A dermoscopic image of a skin lesion: 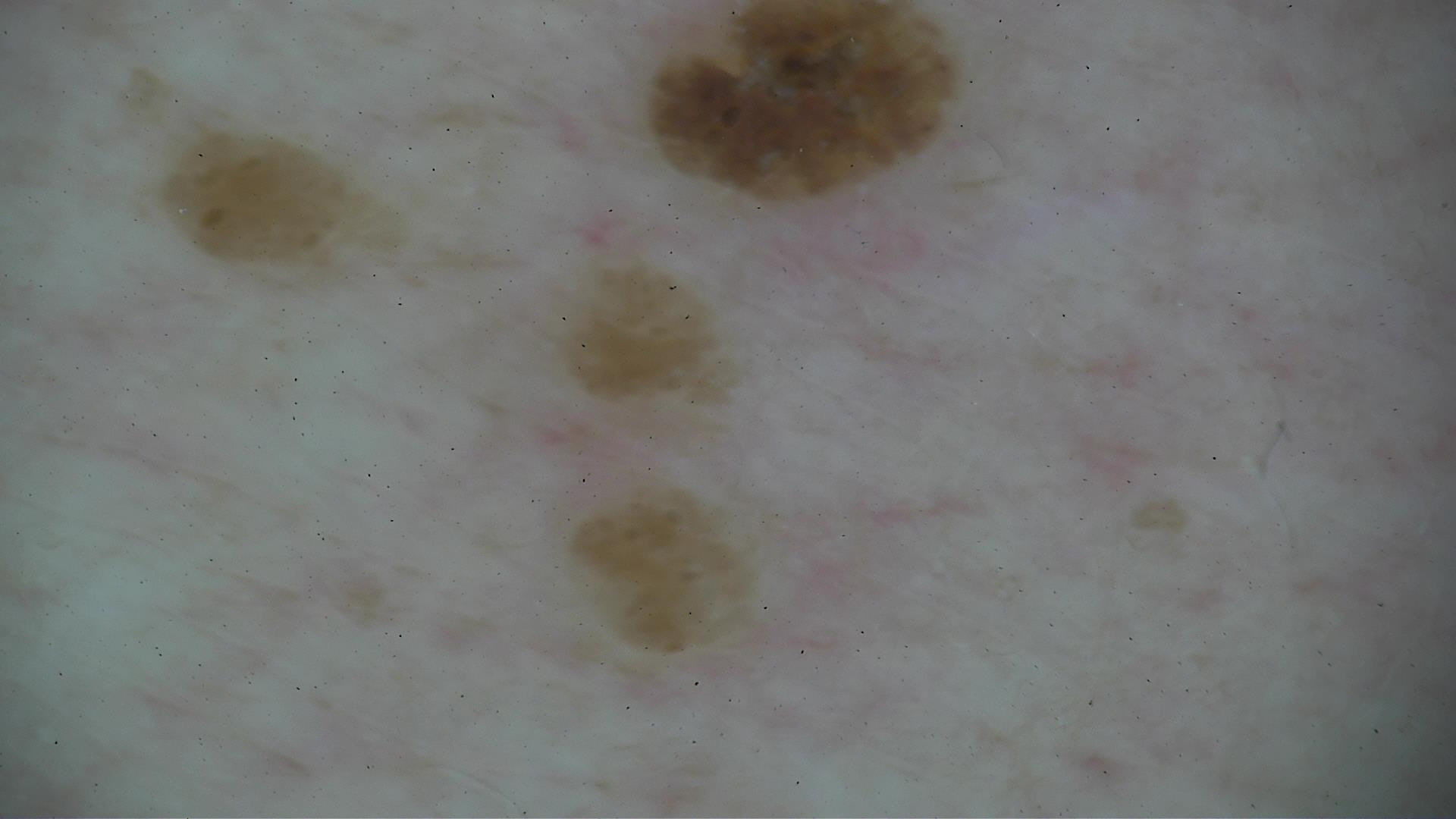The diagnosis was a keratinocytic, benign lesion — a seborrheic keratosis.